Dermoscopy of a skin lesion: 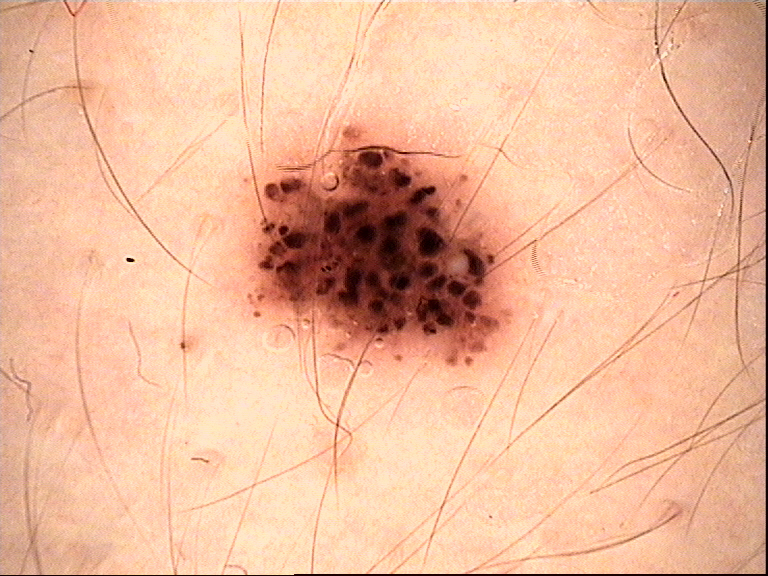label = dysplastic compound nevus (expert consensus).